A dermoscopic image of a skin lesion.
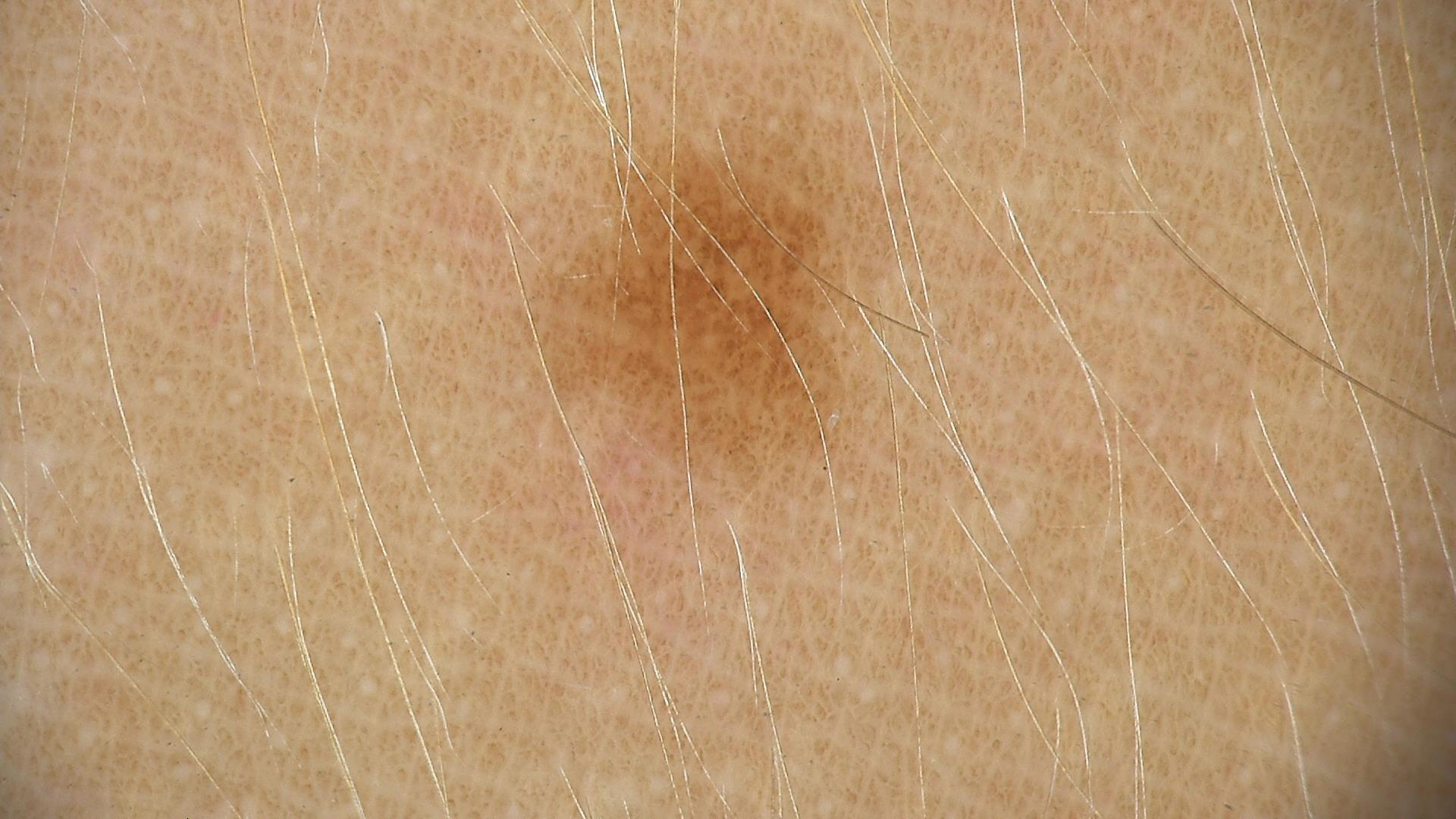{
  "diagnosis": {
    "name": "dysplastic junctional nevus",
    "code": "jd",
    "malignancy": "benign",
    "super_class": "melanocytic",
    "confirmation": "expert consensus"
  }
}